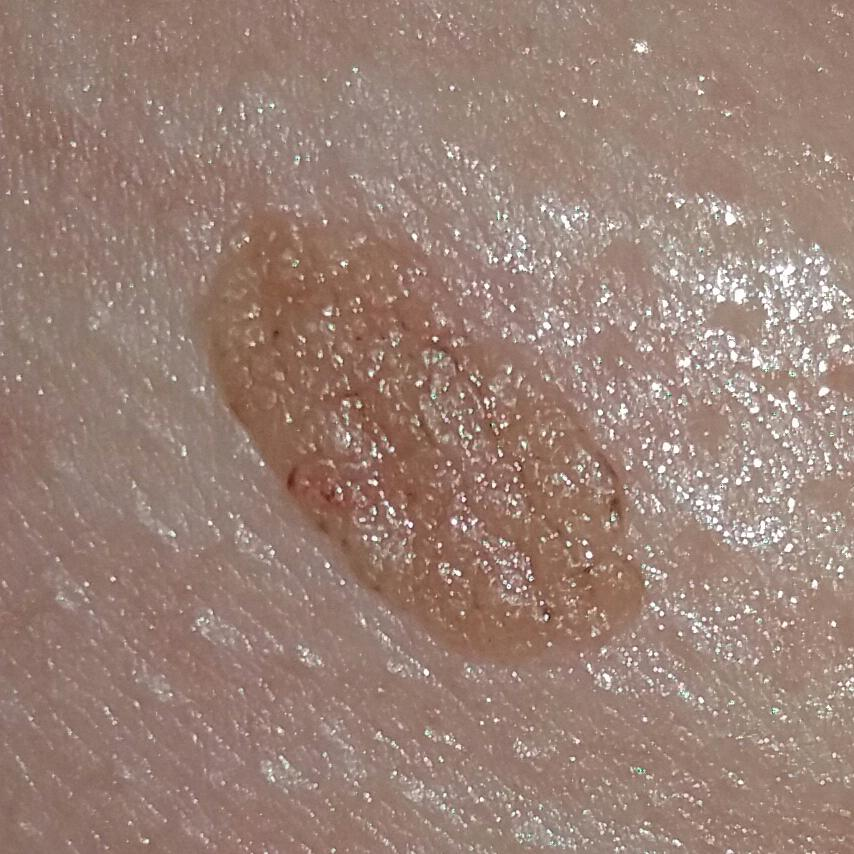A clinical photograph of a skin lesion.
A patient in their 50s.
The patient reports that the lesion is elevated.
The diagnostic impression was a nevus.